A dermoscopy image of a single skin lesion.
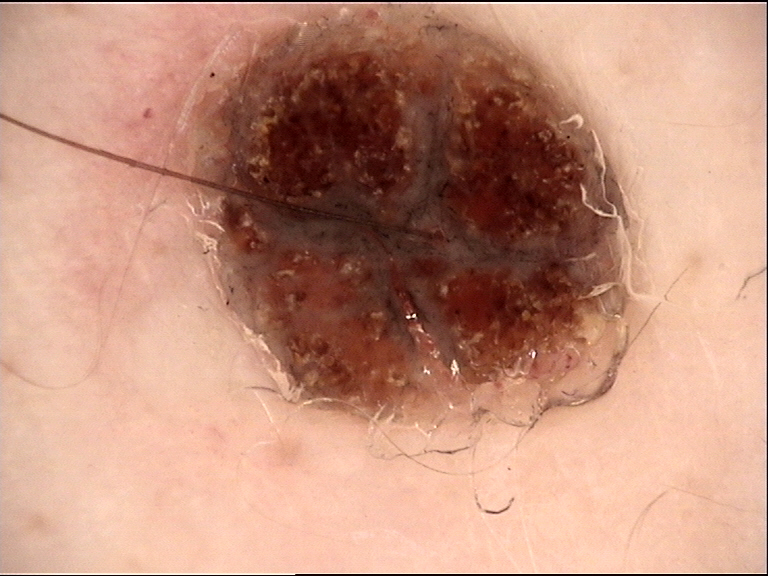diagnostic label=compound nevus (expert consensus)